A clinical photo of a skin lesion taken with a smartphone. A patient in their 50s — 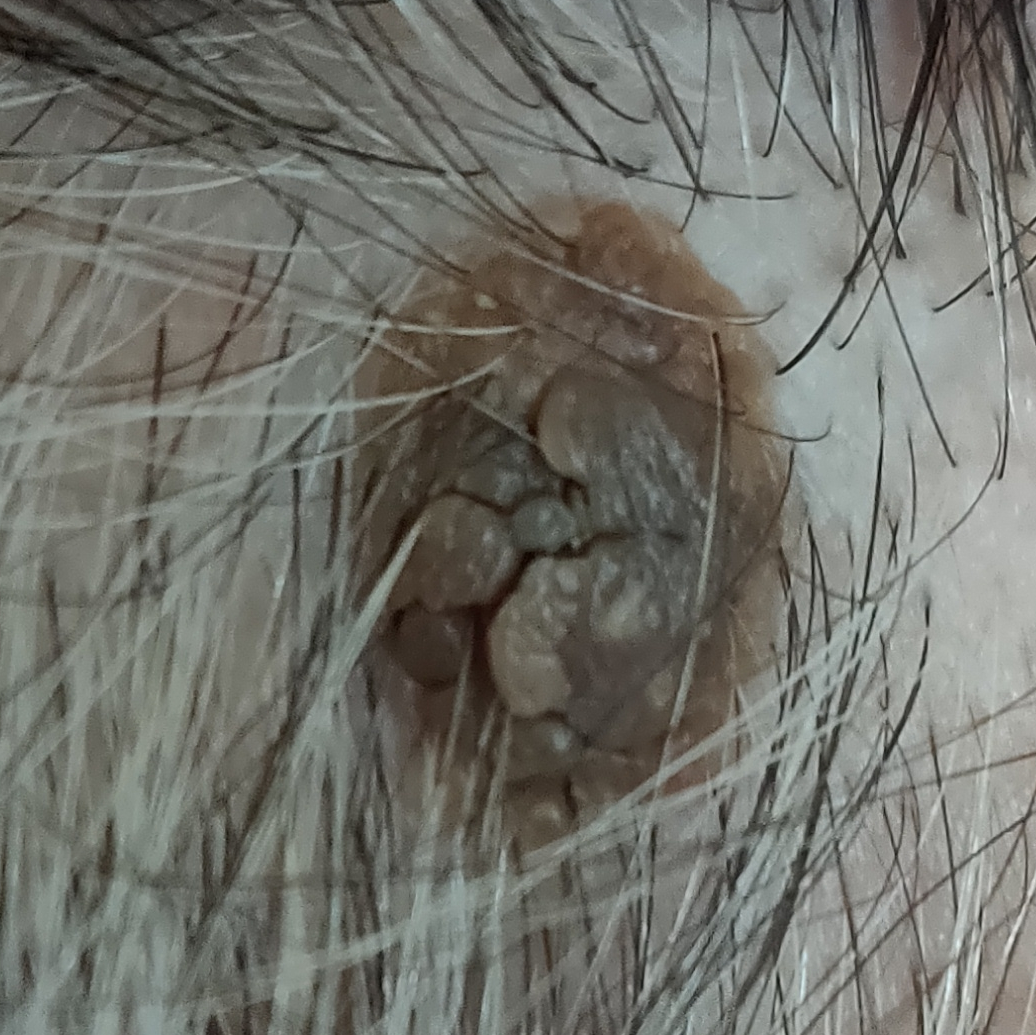Summary: Located on the face. By the patient's account, the lesion is elevated, has grown, has changed, and itches, but has not bled. Conclusion: The clinical impression was a seborrheic keratosis.